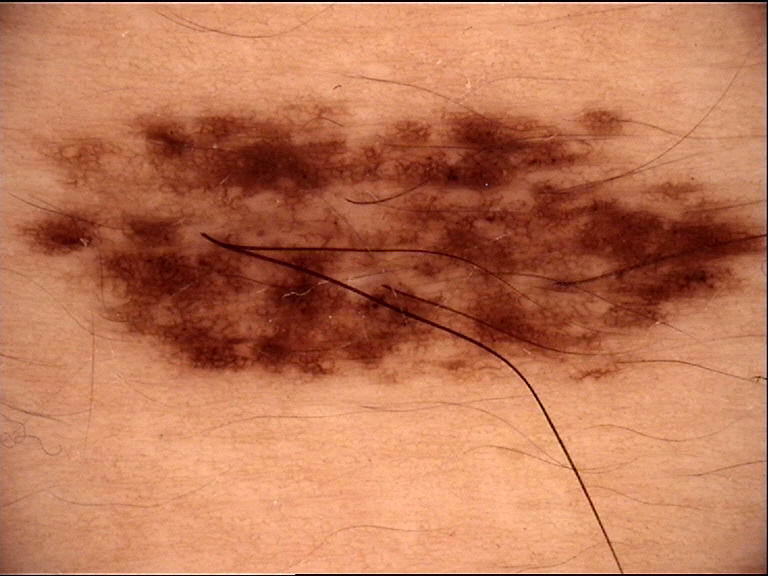Q: What kind of image is this?
A: dermoscopy
Q: What is this lesion?
A: dysplastic junctional nevus (expert consensus)